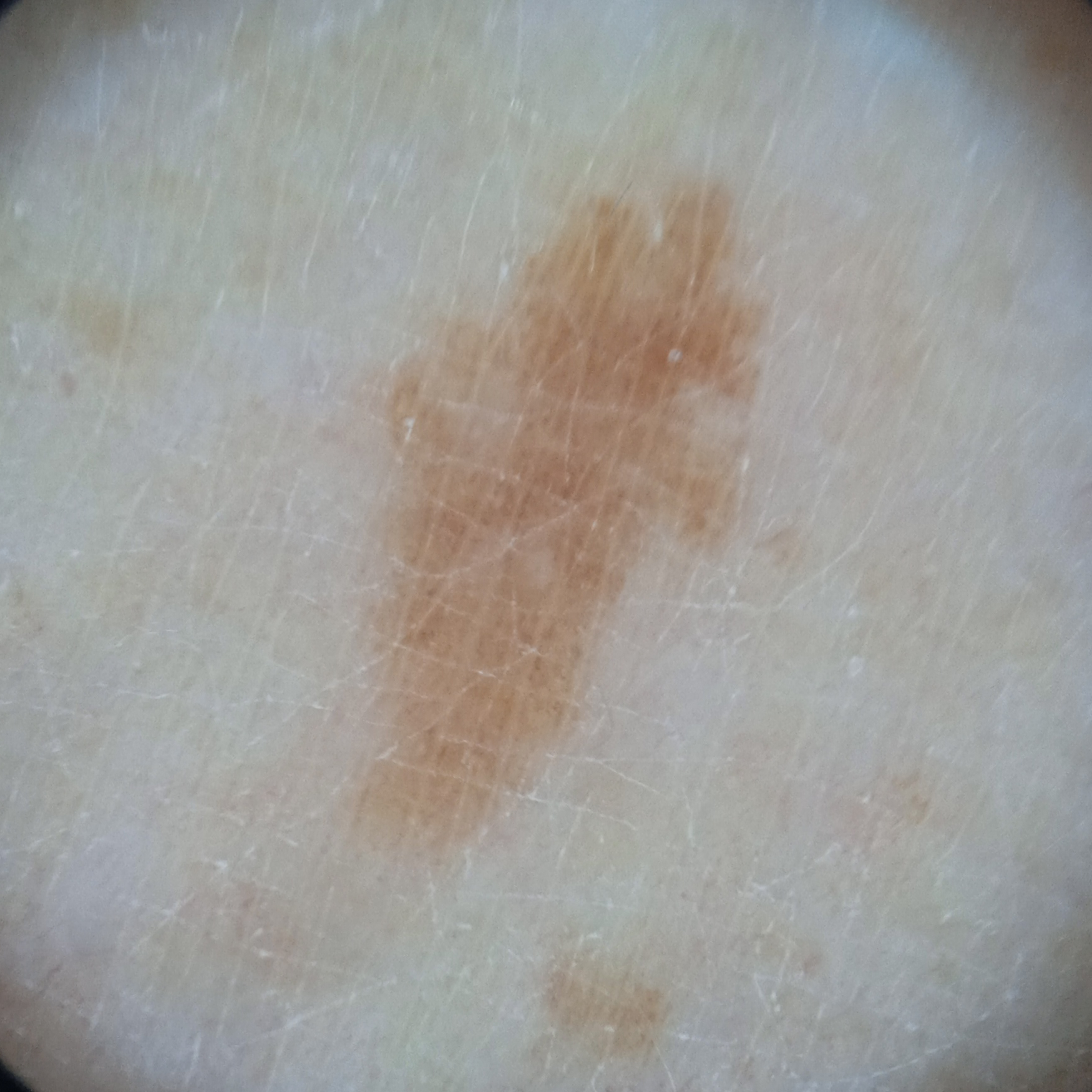By self-report, a personal history of cancer, a personal history of skin cancer, and no sunbed use. A dermoscopy image of a skin lesion. The patient says their skin tans without first burning. A female patient aged 75. Acquired for a research image collection, with no referral diagnosis. A moderate number of moles by the patient's own estimate. Located on a leg. The consensus diagnosis for this lesion was a melanocytic nevus.